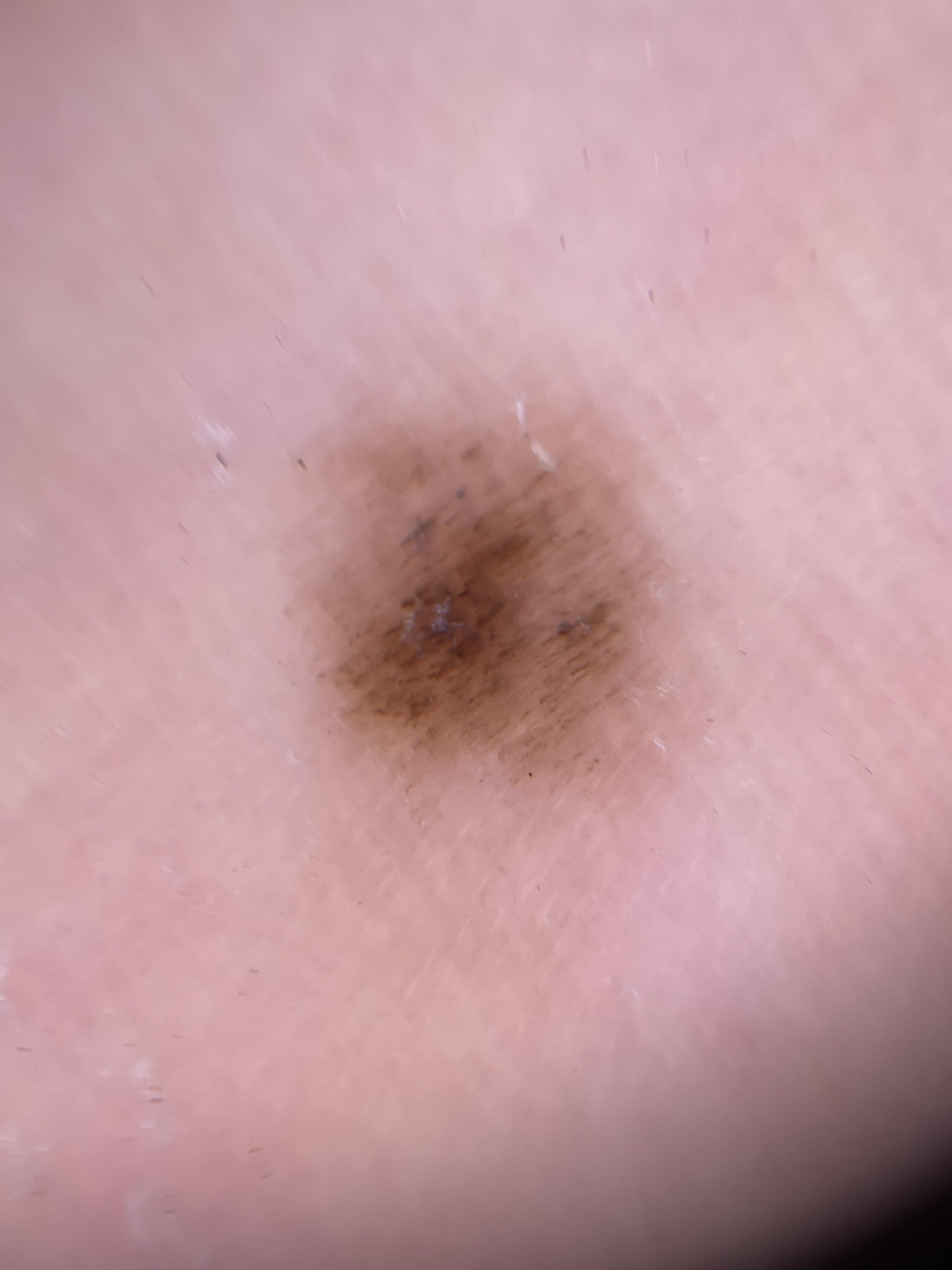A skin lesion imaged with contact-polarized dermoscopy. The lesion involves an acral site (palms or soles). The clinical assessment was a nevus.